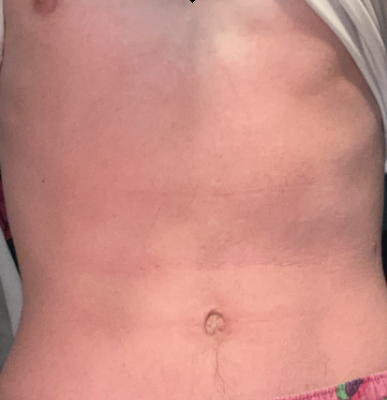No differential diagnosis could be assigned on photographic review.